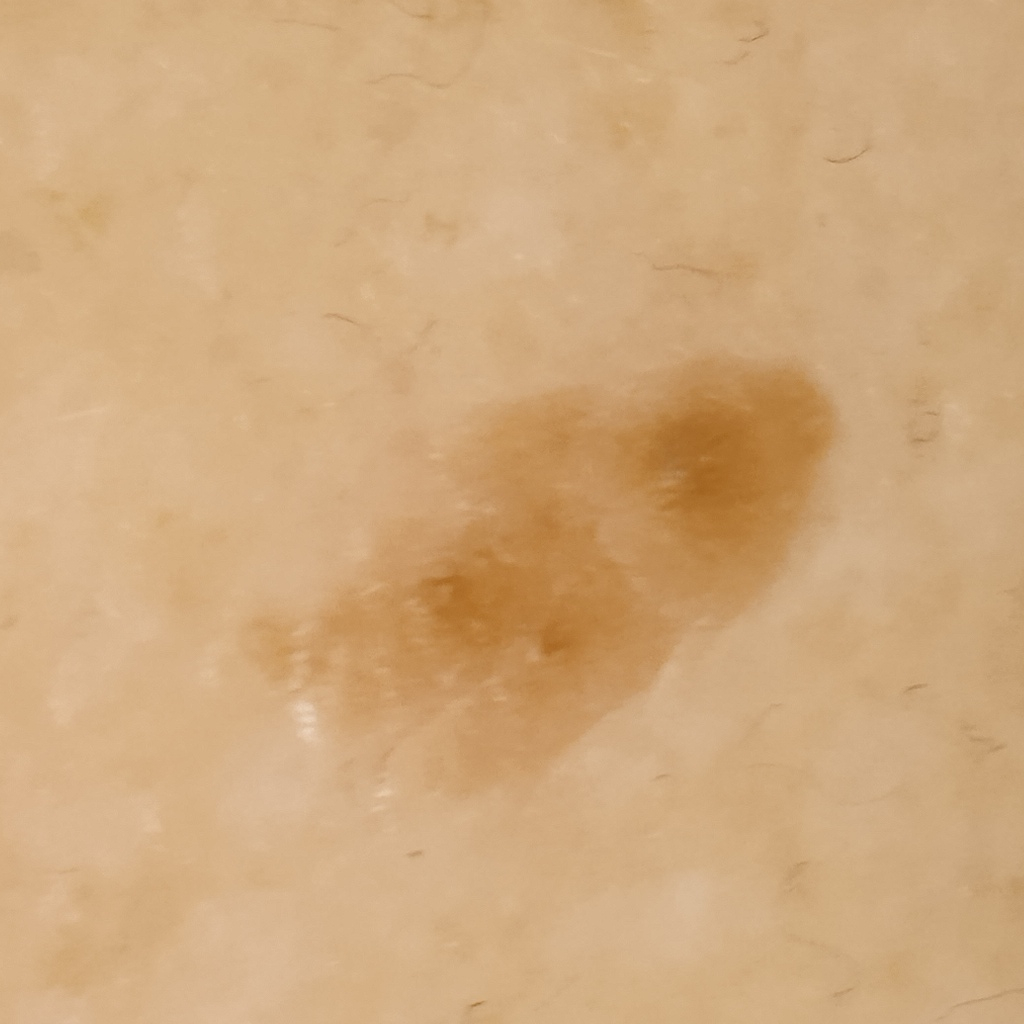referral: research study (no referral diagnosis), sun reaction: skin reddens with sun exposure, modality: clinical photo, anatomic site: the torso, diameter: 9.1 mm, diagnosis: seborrheic keratosis (dermatologist consensus).